A dermoscopic close-up of a skin lesion.
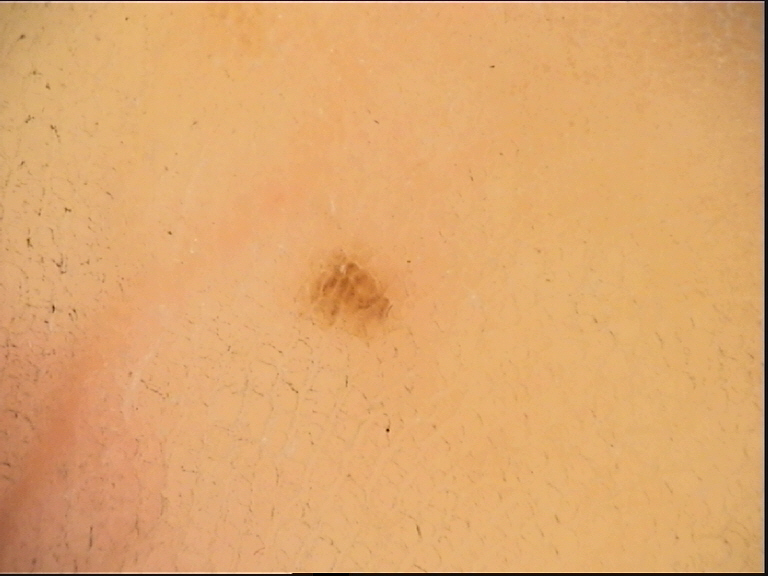Conclusion:
The diagnostic label was a banal lesion — an acral junctional nevus.